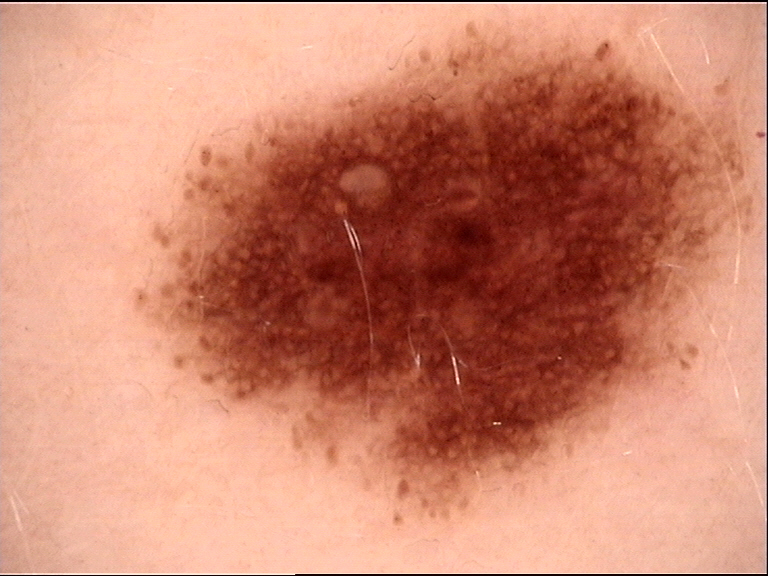Q: What is this lesion?
A: dysplastic junctional nevus (expert consensus)